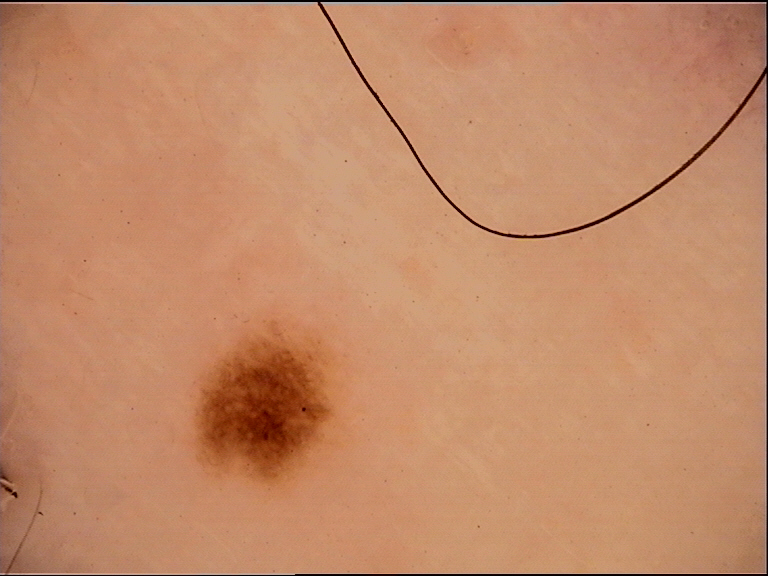A dermoscopy image of a single skin lesion. The diagnostic label was a dysplastic junctional nevus.